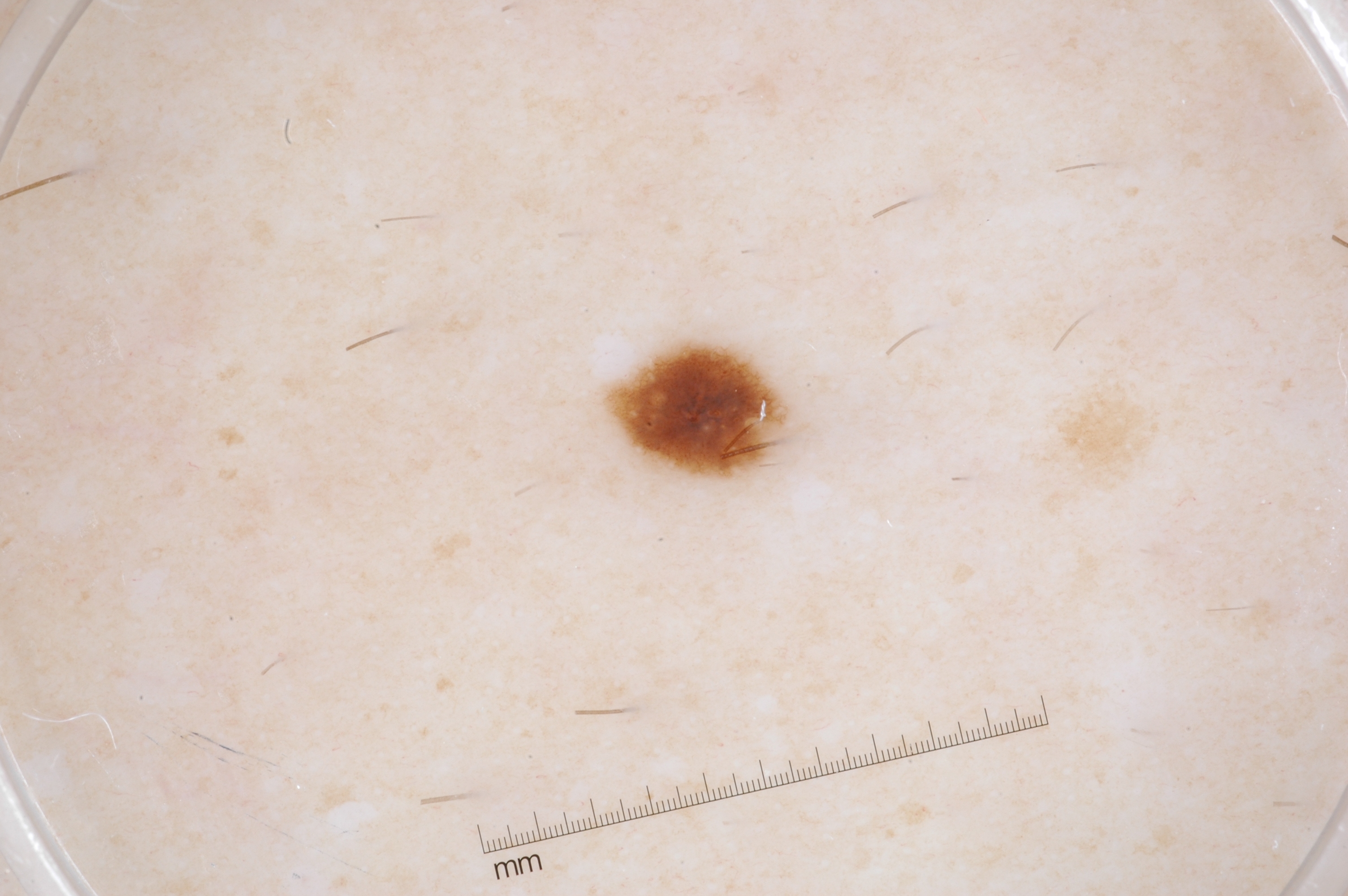Findings: A dermoscopic image of a skin lesion. A female subject, roughly 35 years of age. The dermoscopic pattern shows pigment network; no milia-like cysts, negative network, or streaks. In (x1, y1, x2, y2) order, the lesion is located at [603,341,789,479]. Conclusion: Consistent with a melanocytic nevus.